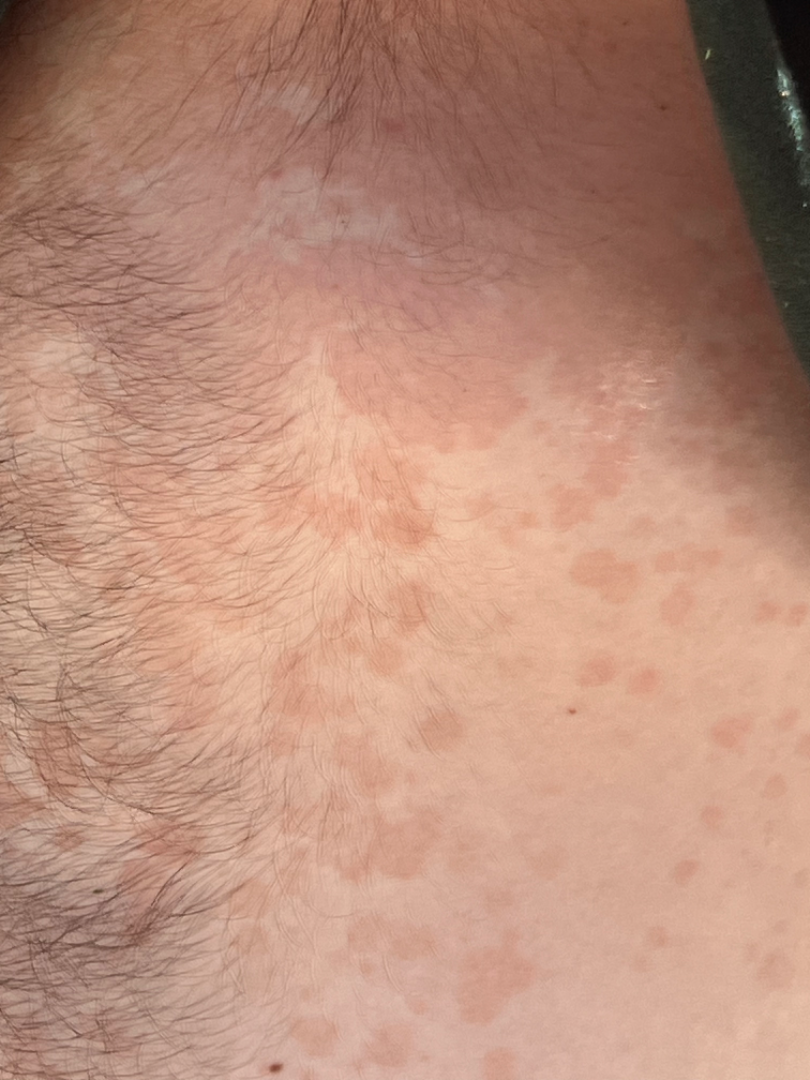Background:
This image was taken at an angle. The subject is 18–29, male. The affected area is the front of the torso and back of the torso.
Findings:
The impression is Tinea Versicolor.